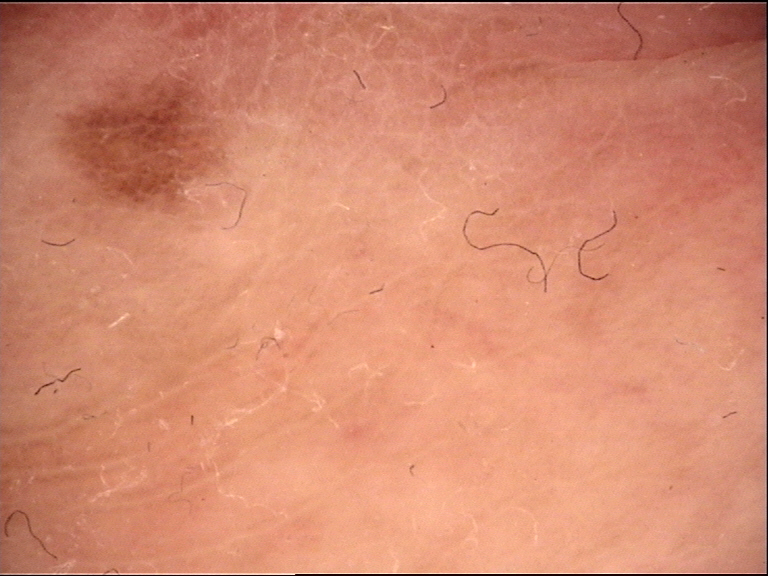A dermoscopic close-up of a skin lesion. Diagnosed as a dysplastic junctional nevus.